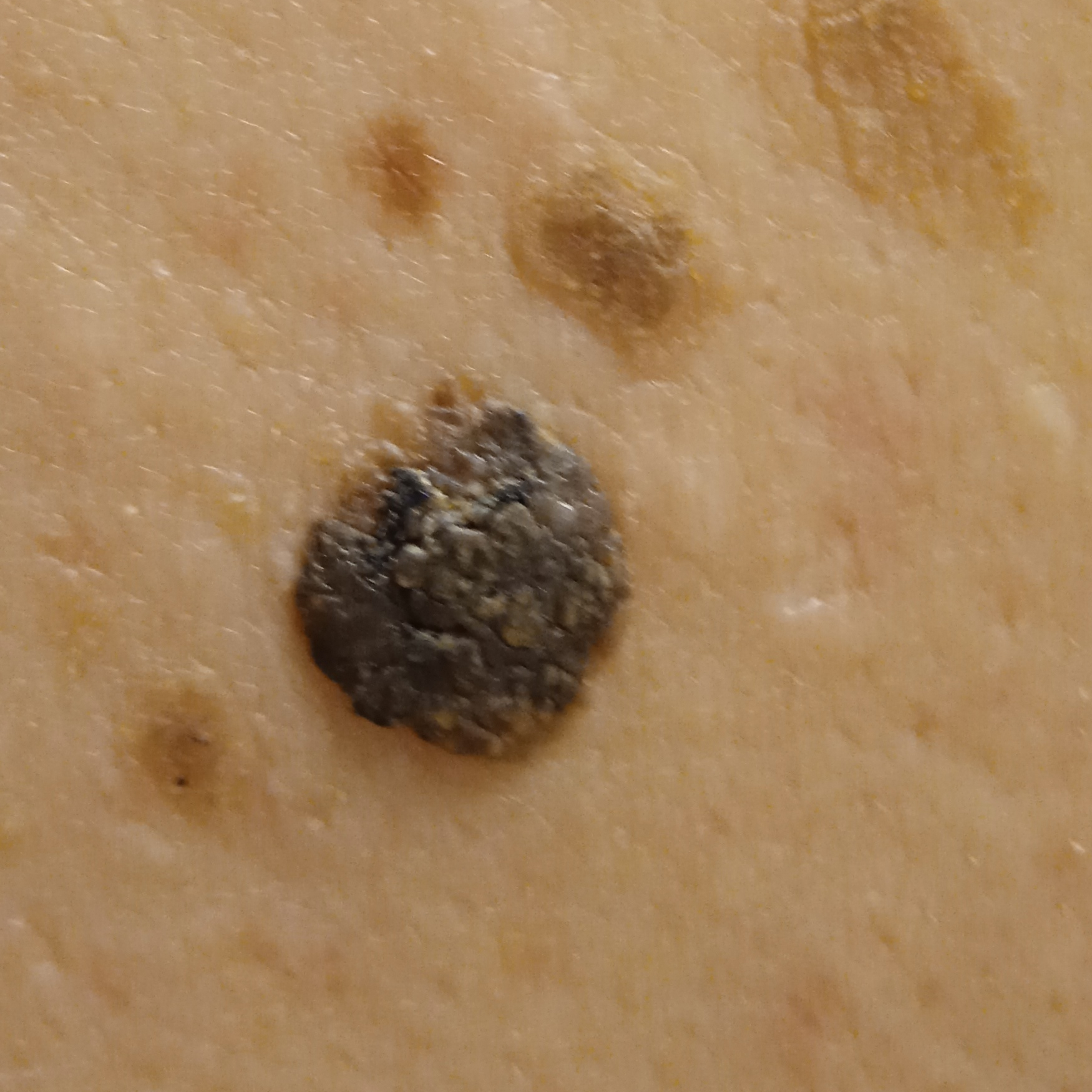A moderate number of moles by the patient's own estimate. A male patient 65 years old. On a questionnaire the patient reported a personal history of cancer and no immunosuppression. Acquired for a research image collection, with no referral diagnosis. A clinical photograph showing a skin lesion. Located on the back. Measuring roughly 12 mm. The diagnostic impression was a seborrheic keratosis.